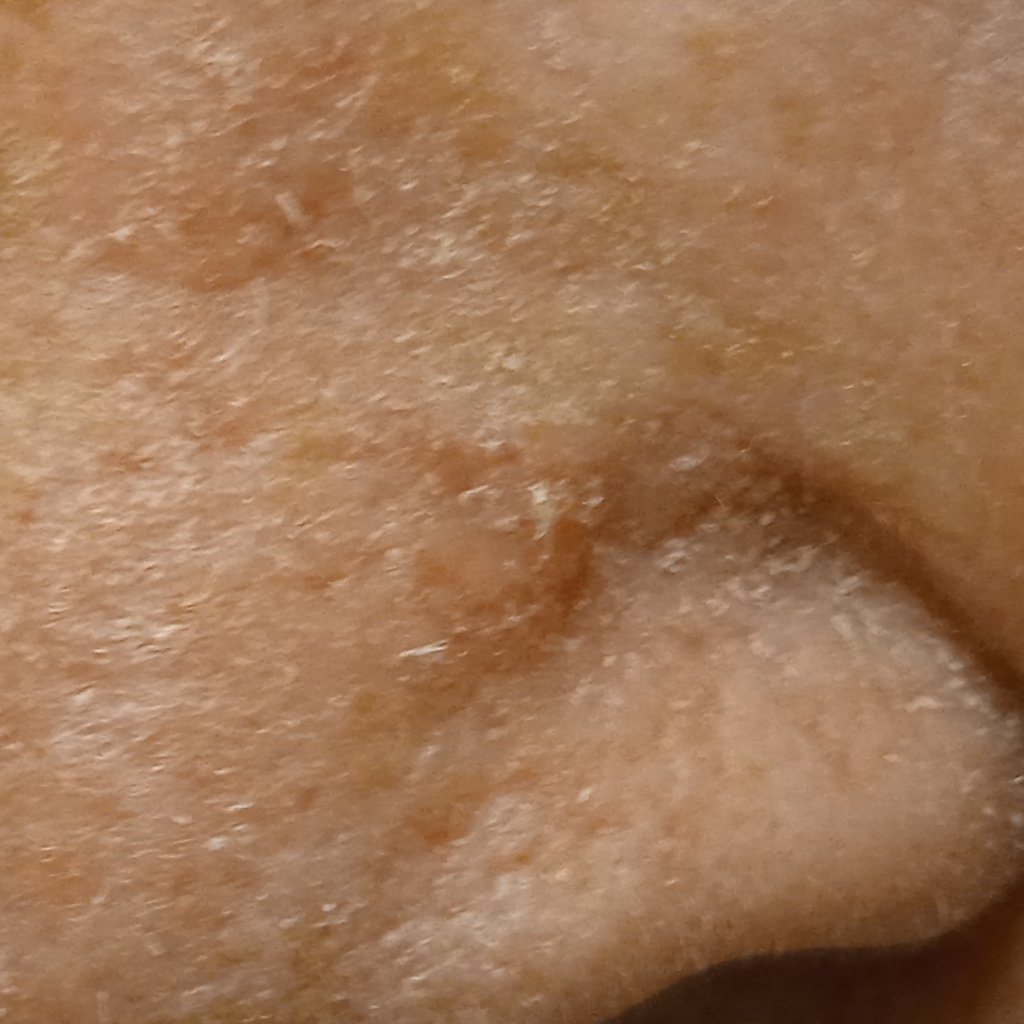Q: How does the patient's skin react to sun?
A: skin tans without first burning
Q: What is the referral context?
A: research study (no referral diagnosis)
Q: What are the relevant risk factors?
A: a personal history of cancer, a family history of skin cancer
Q: Patient demographics?
A: female, aged 92
Q: What kind of image is this?
A: clinical photo
Q: Where is the lesion?
A: the face
Q: How large is the lesion?
A: 7 mm
Q: What was the diagnosis?
A: basal cell carcinoma (dermatologist consensus)